A male subject in their mid-70s. A dermoscopy image of a single skin lesion: 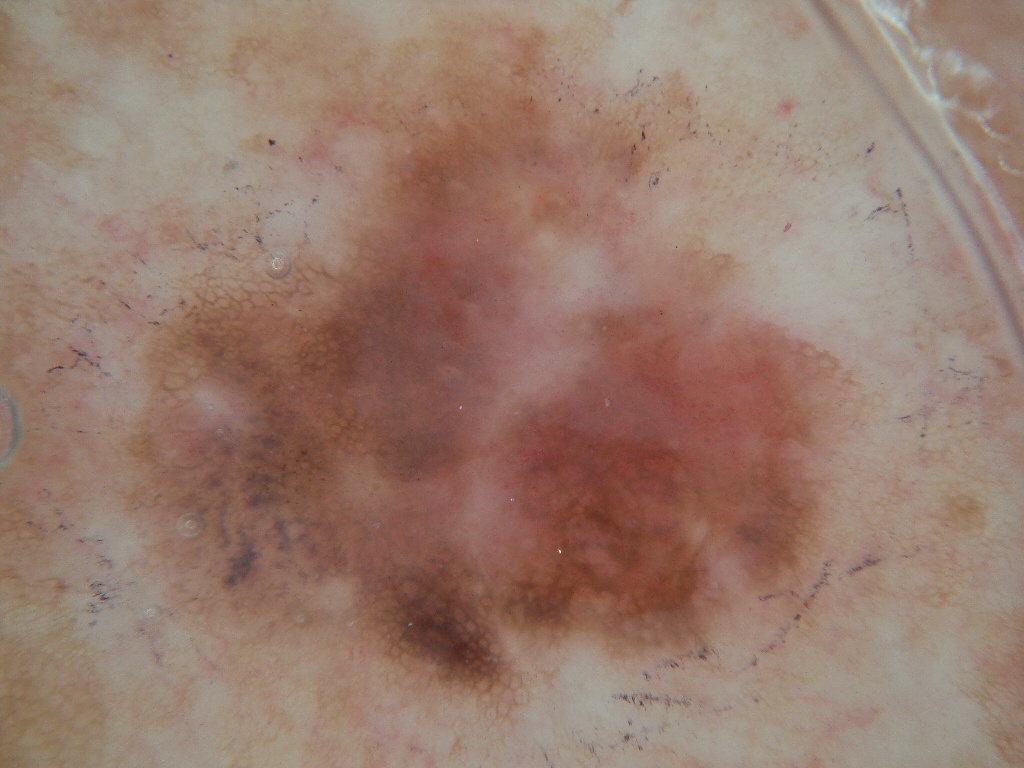Case summary: On dermoscopy, the lesion shows pigment network. The lesion stretches across essentially the whole frame. Conclusion: On biopsy, the diagnosis was a melanoma, a malignant lesion.